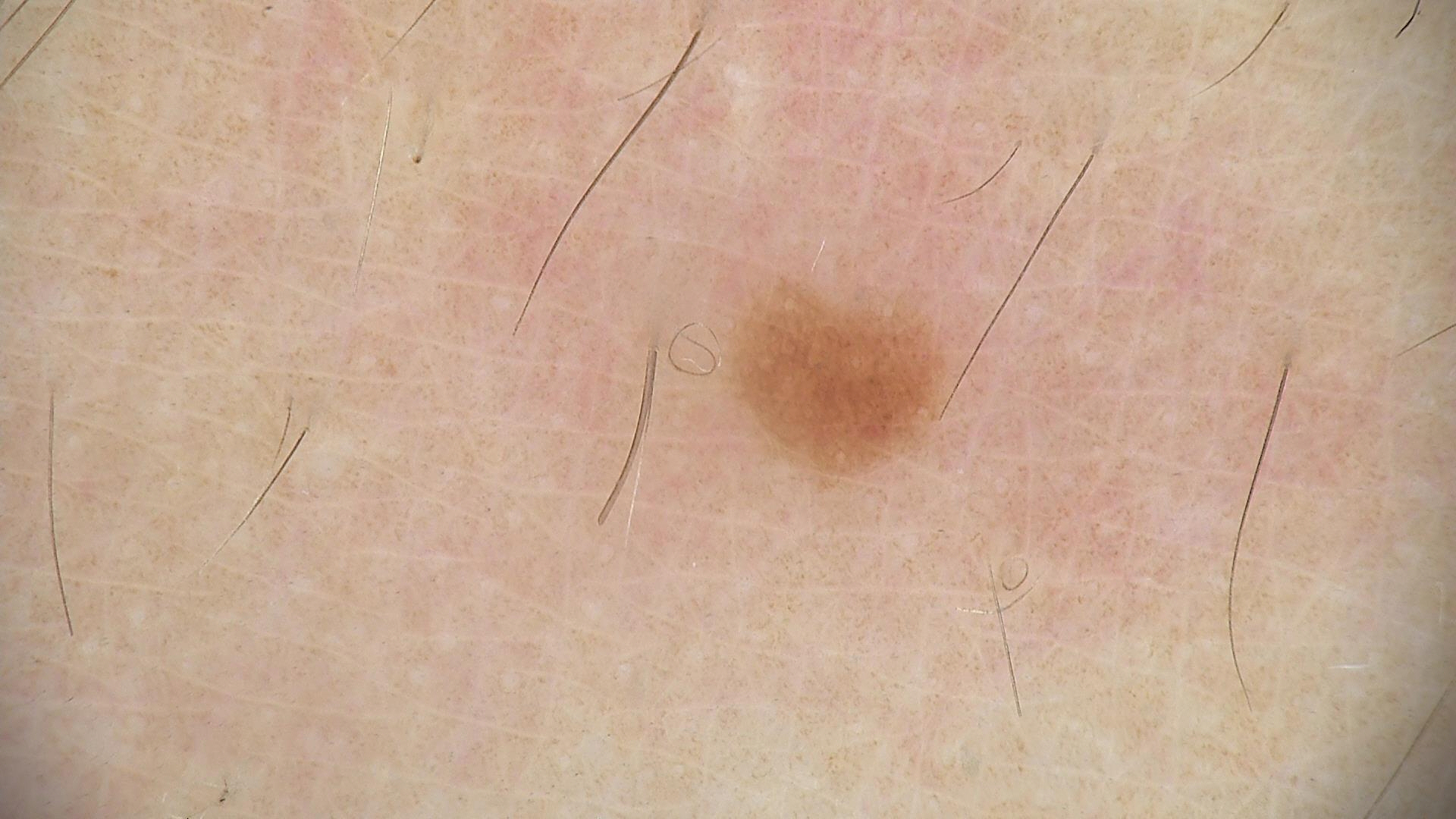Q: What kind of image is this?
A: dermatoscopy
Q: What was the diagnostic impression?
A: dysplastic junctional nevus (expert consensus)